A close-up photograph — 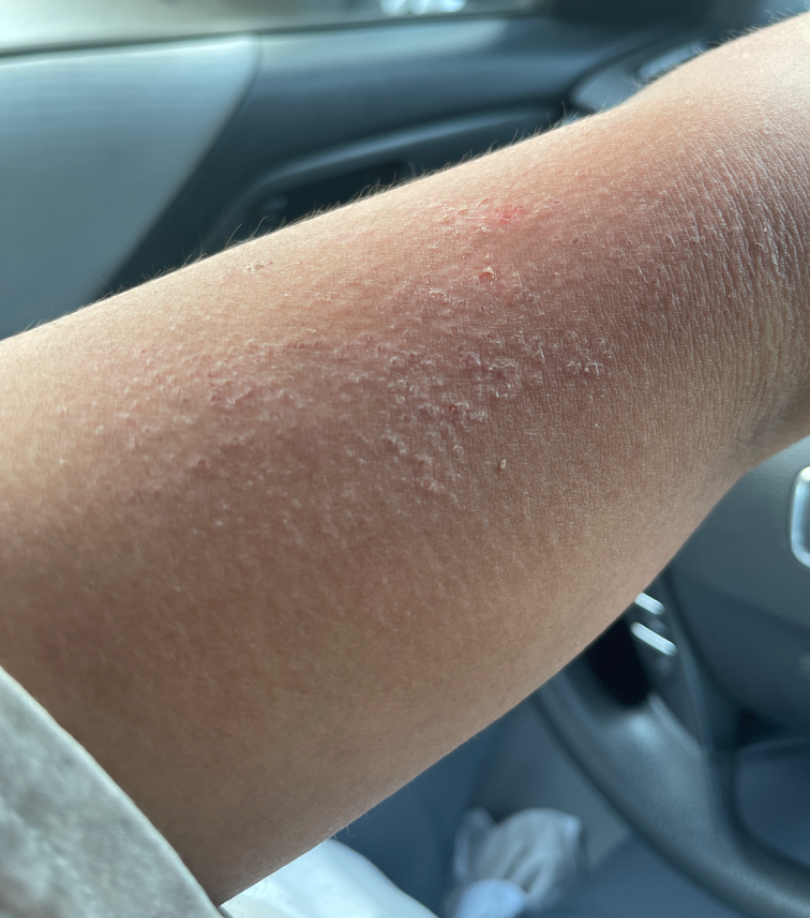Notes:
• impression: most likely Eczema; an alternative is Psoriasis; with consideration of Lichen Simplex Chronicus